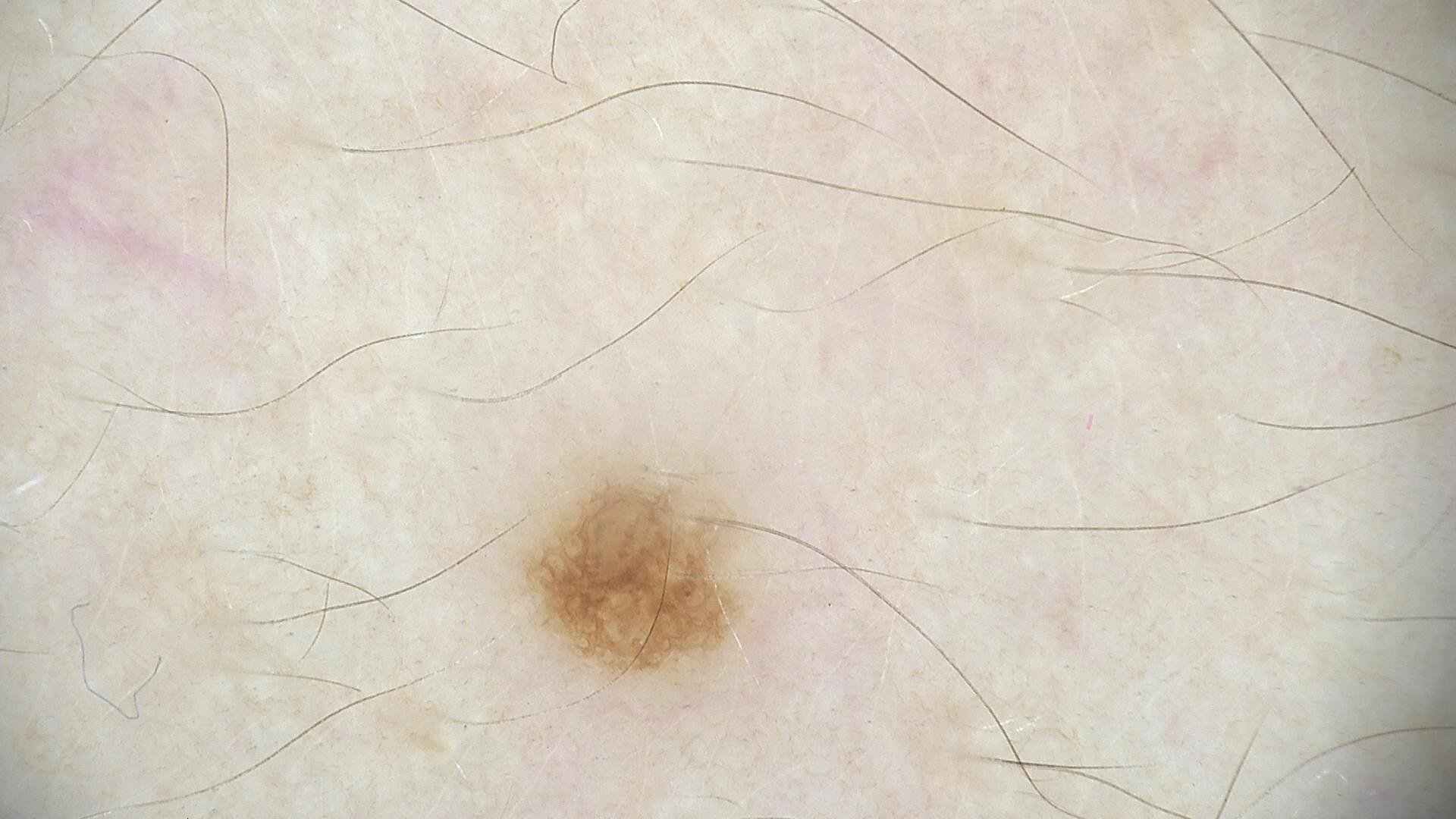The diagnostic label was a dysplastic junctional nevus.